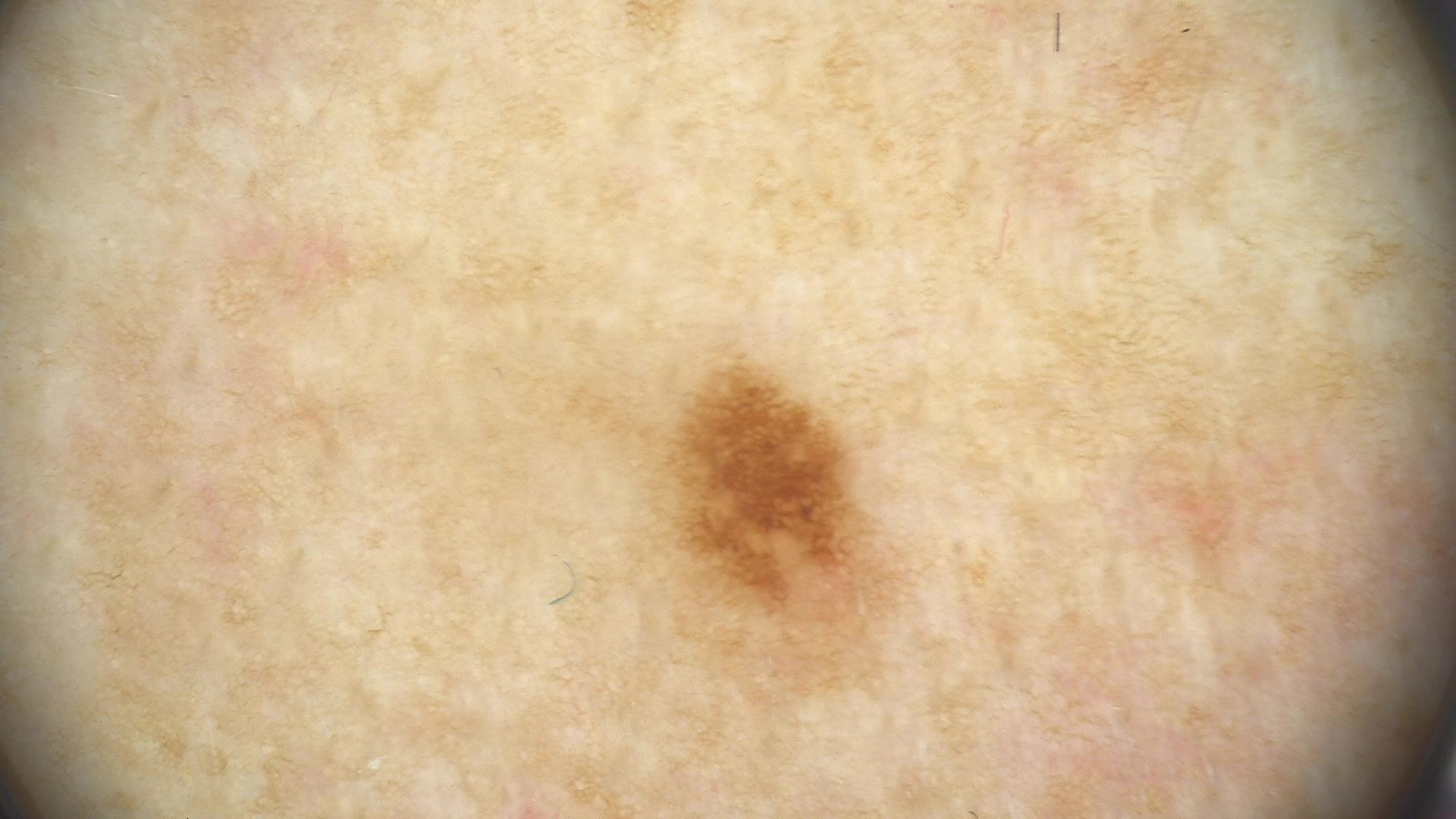image: dermatoscopy, diagnostic label: dysplastic junctional nevus (expert consensus).